A male patient roughly 40 years of age · the patient is FST III · a dermoscopic close-up of a skin lesion · the chart notes melanoma in a first-degree relative but no prior melanoma.
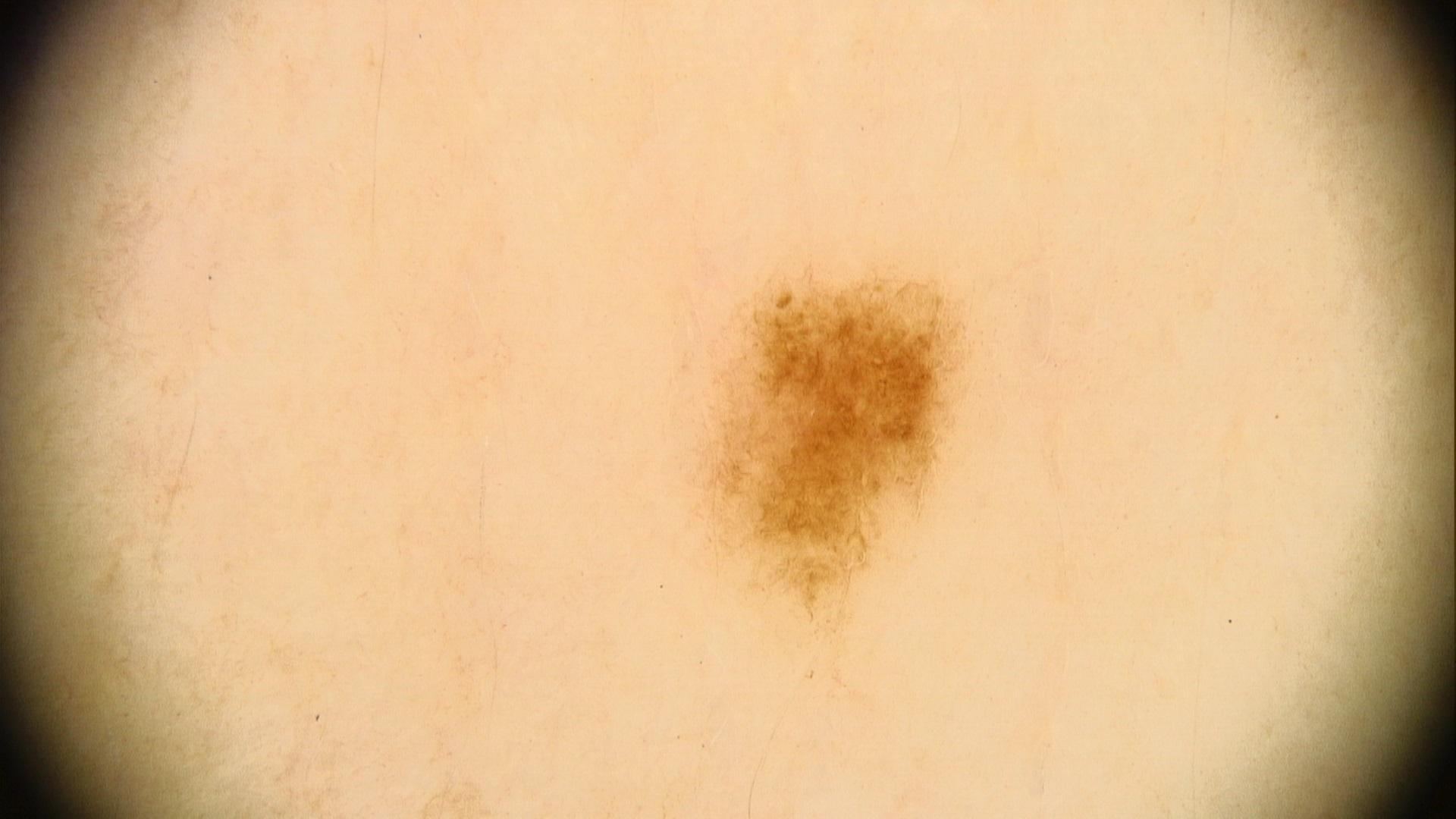The lesion is on the anterior trunk.
The clinical impression was a lesion of melanocytic lineage — a nevus.